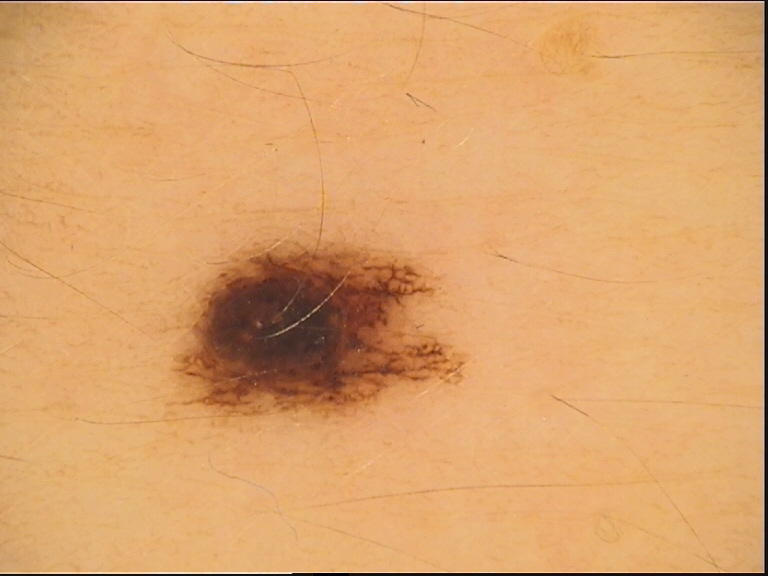<dermoscopy>
<diagnosis>
<name>dysplastic compound nevus</name>
<code>cd</code>
<malignancy>benign</malignancy>
<super_class>melanocytic</super_class>
<confirmation>expert consensus</confirmation>
</diagnosis>
</dermoscopy>